The contributor is a female aged 30–39 · the photo was captured at an angle · located on the arm:
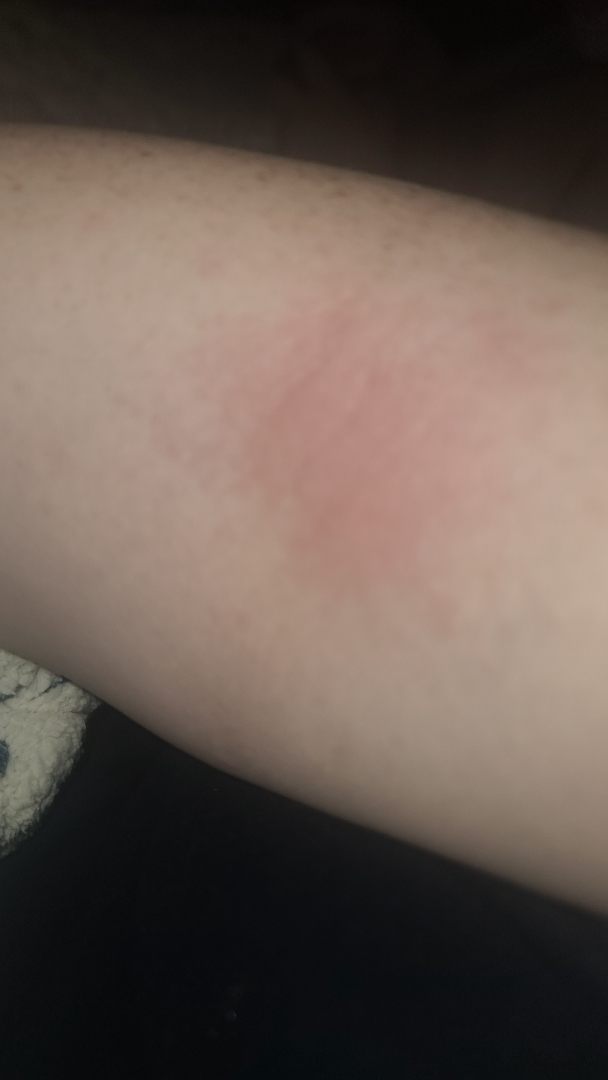The patient indicates itching.
Self-categorized by the patient as a rash.
The patient indicates the lesion is raised or bumpy.
The patient indicates the condition has been present for one to four weeks.
On remote dermatologist review: the favored diagnosis is Eczema; possibly Tinea; also on the differential is Irritant Contact Dermatitis.